A female patient roughly 40 years of age, this is a dermoscopic photograph of a skin lesion.
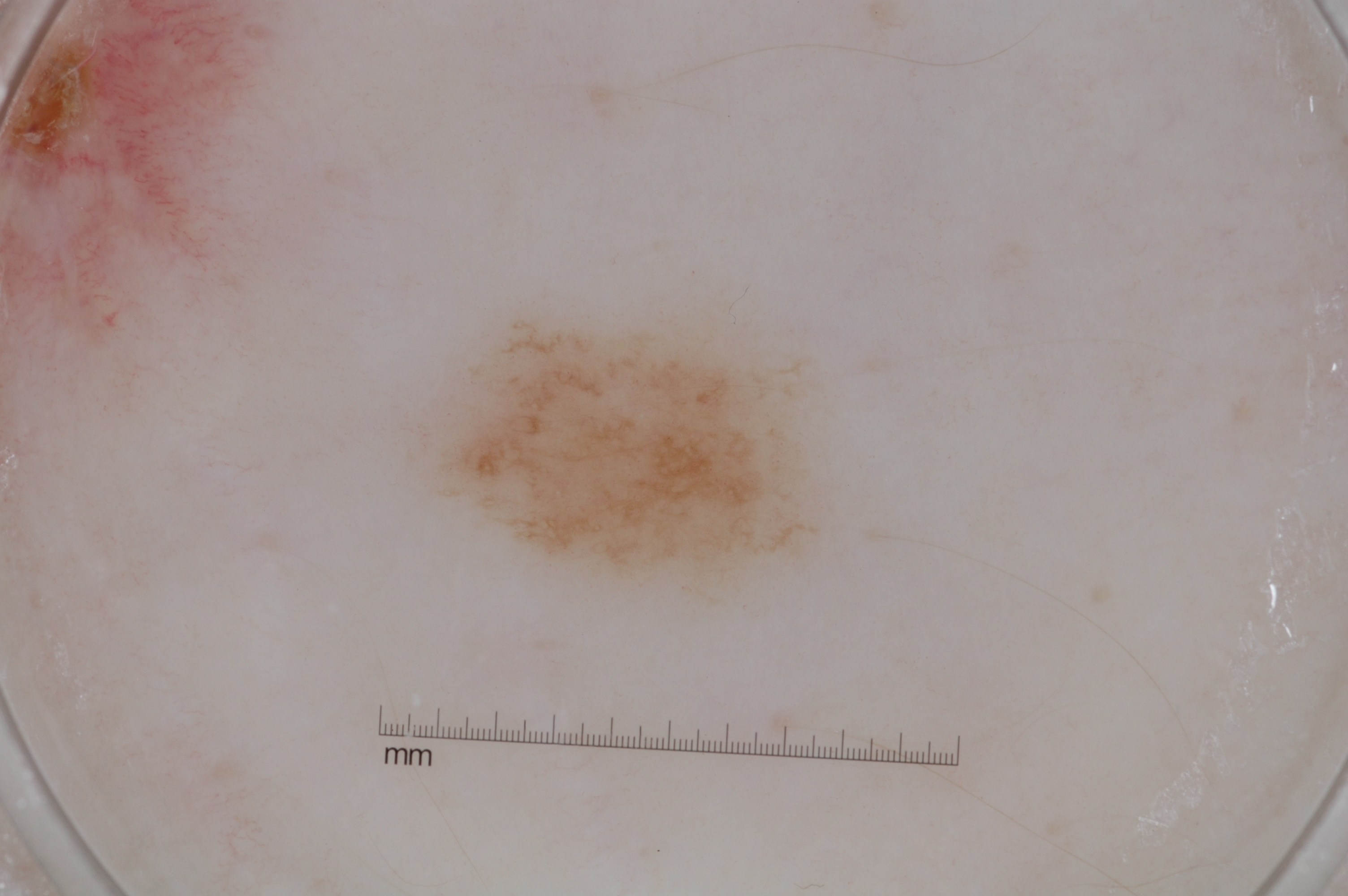lesion bbox: [417, 321, 862, 610]; extent: small; features: pigment network; assessment: a melanocytic nevus, a benign lesion.